A skin lesion imaged with a dermatoscope.
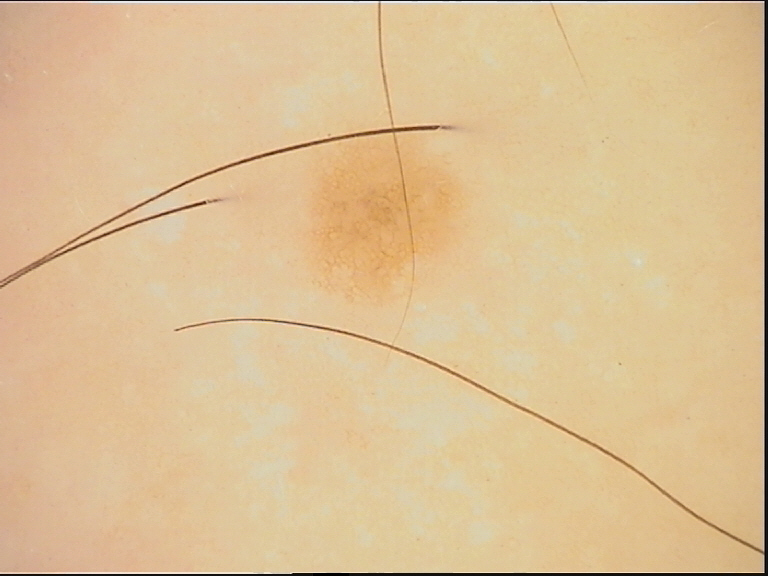category: banal
label: junctional nevus (expert consensus)